This is a close-up image:
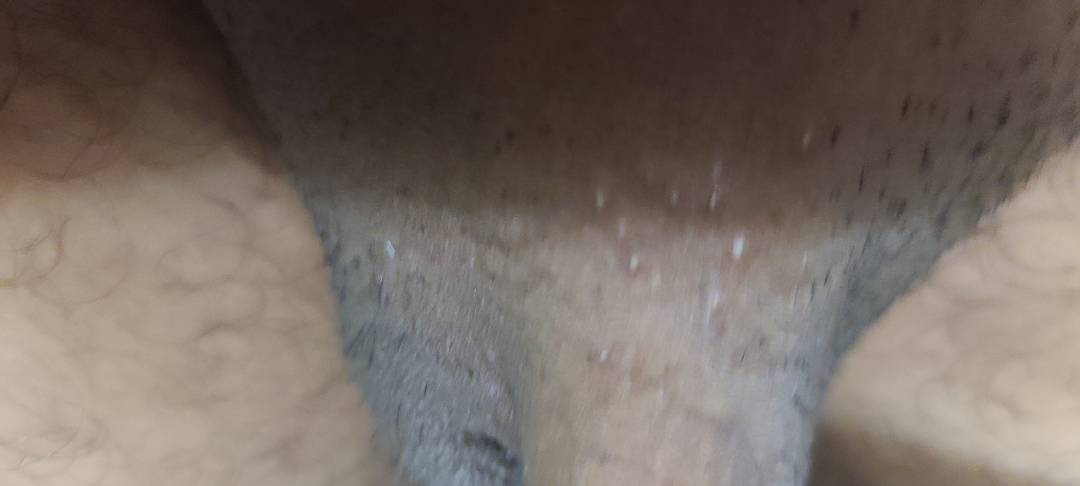{"assessment": "could not be assessed"}